A dermoscopic close-up of a skin lesion:
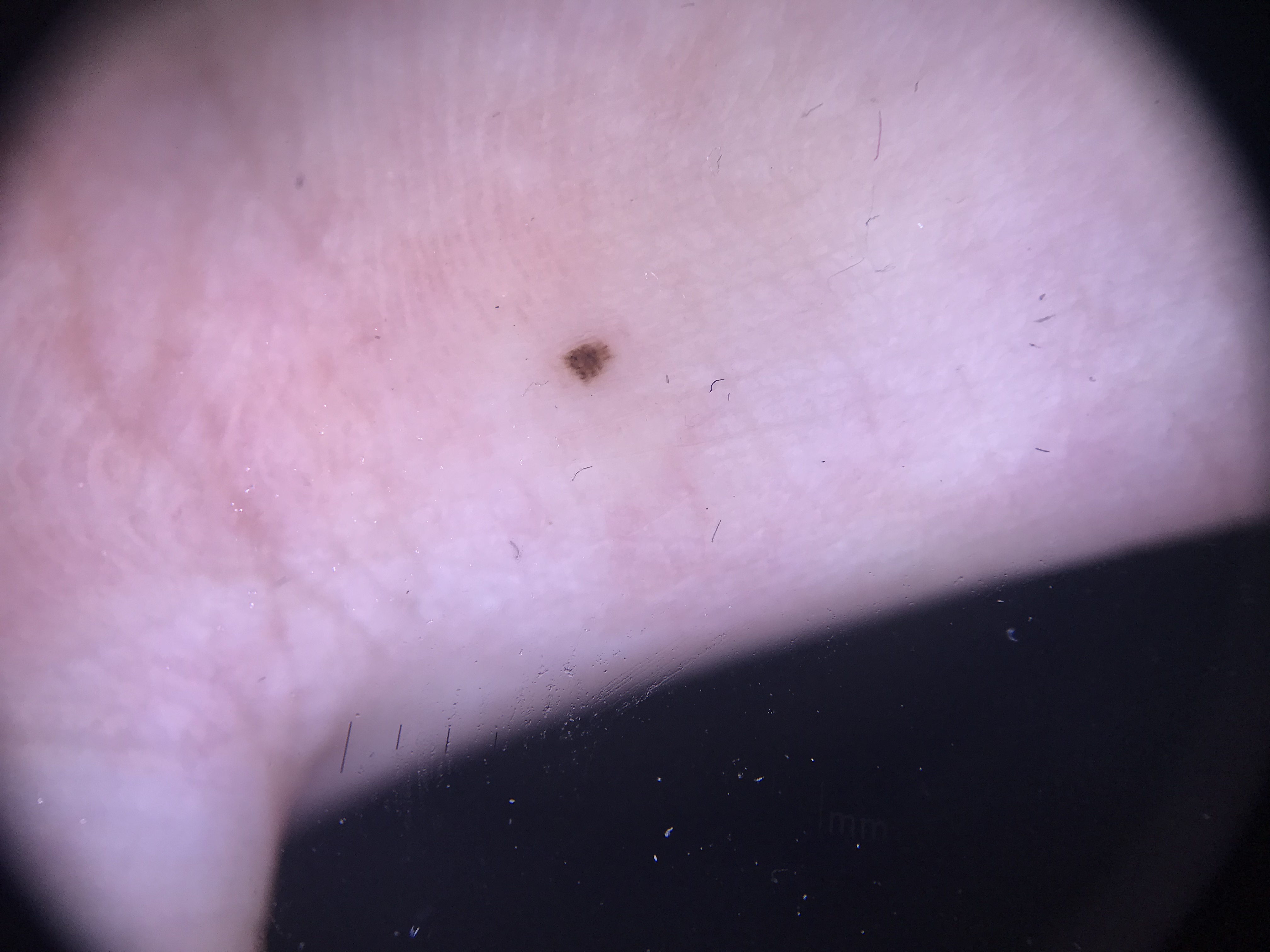label = acral dysplastic junctional nevus (expert consensus)